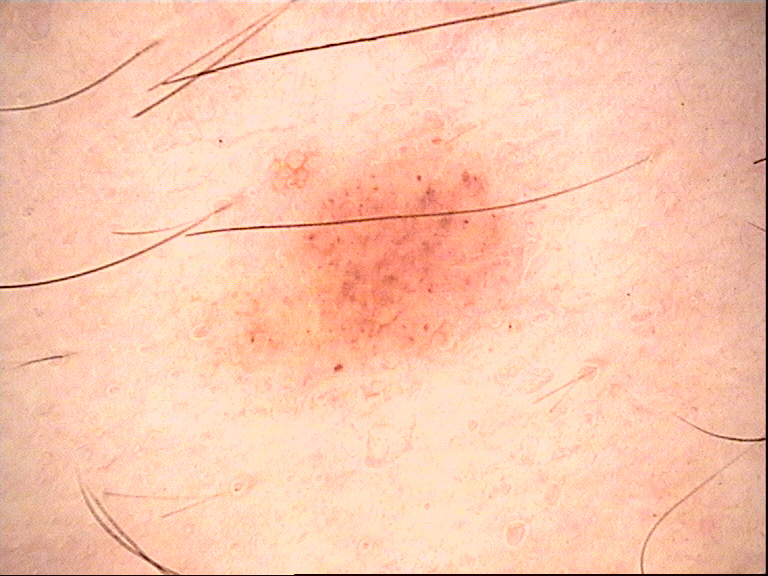Consistent with a dysplastic junctional nevus.